A dermoscopy image of a single skin lesion; a male subject.
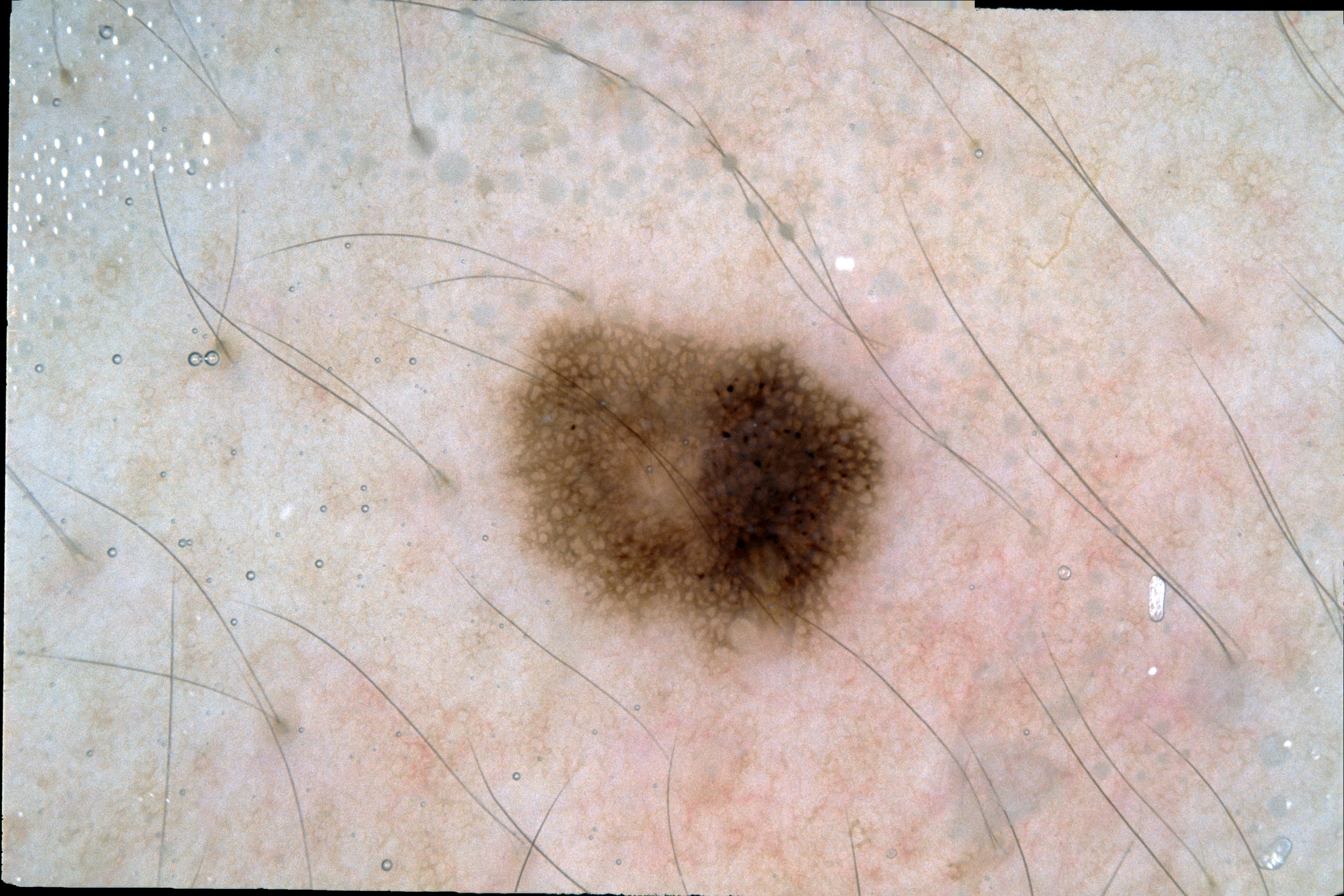Q: What does dermoscopy show?
A: pigment network
Q: Where is the lesion in the image?
A: bbox=[504, 315, 893, 658]
Q: What did the assessment conclude?
A: a melanocytic nevus, a benign lesion